A male patient 65 years old. A macroscopic clinical photograph of a skin lesion. Acquired for a research image collection, with no referral diagnosis. A moderate number of moles by the patient's own estimate. On a questionnaire the patient reported a personal history of cancer. The patient says their skin tans without first burning: 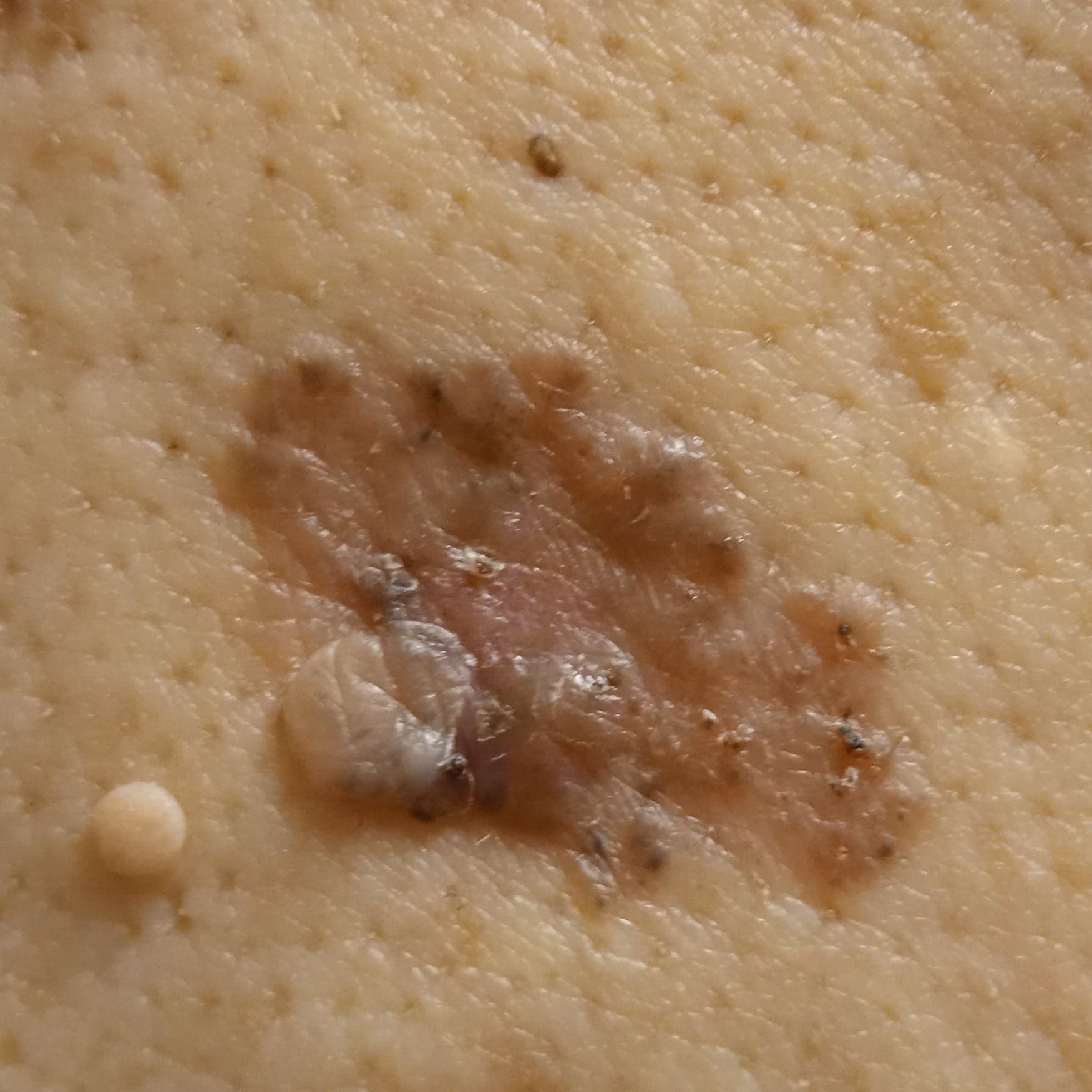Q: Where is the lesion?
A: the back
Q: What was the diagnosis?
A: basal cell carcinoma (dermatologist consensus)